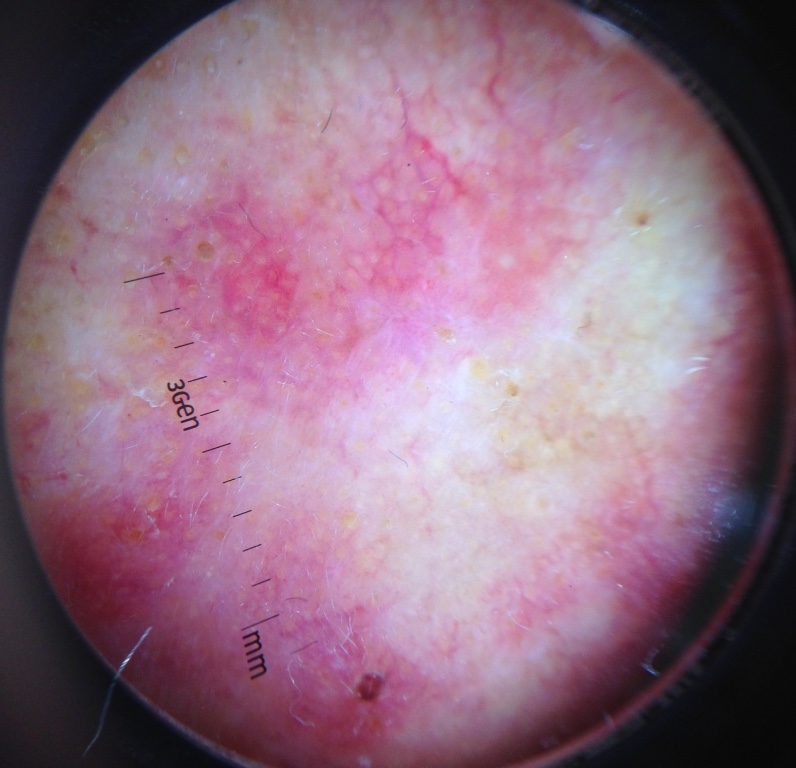label: actinic keratosis (expert consensus)